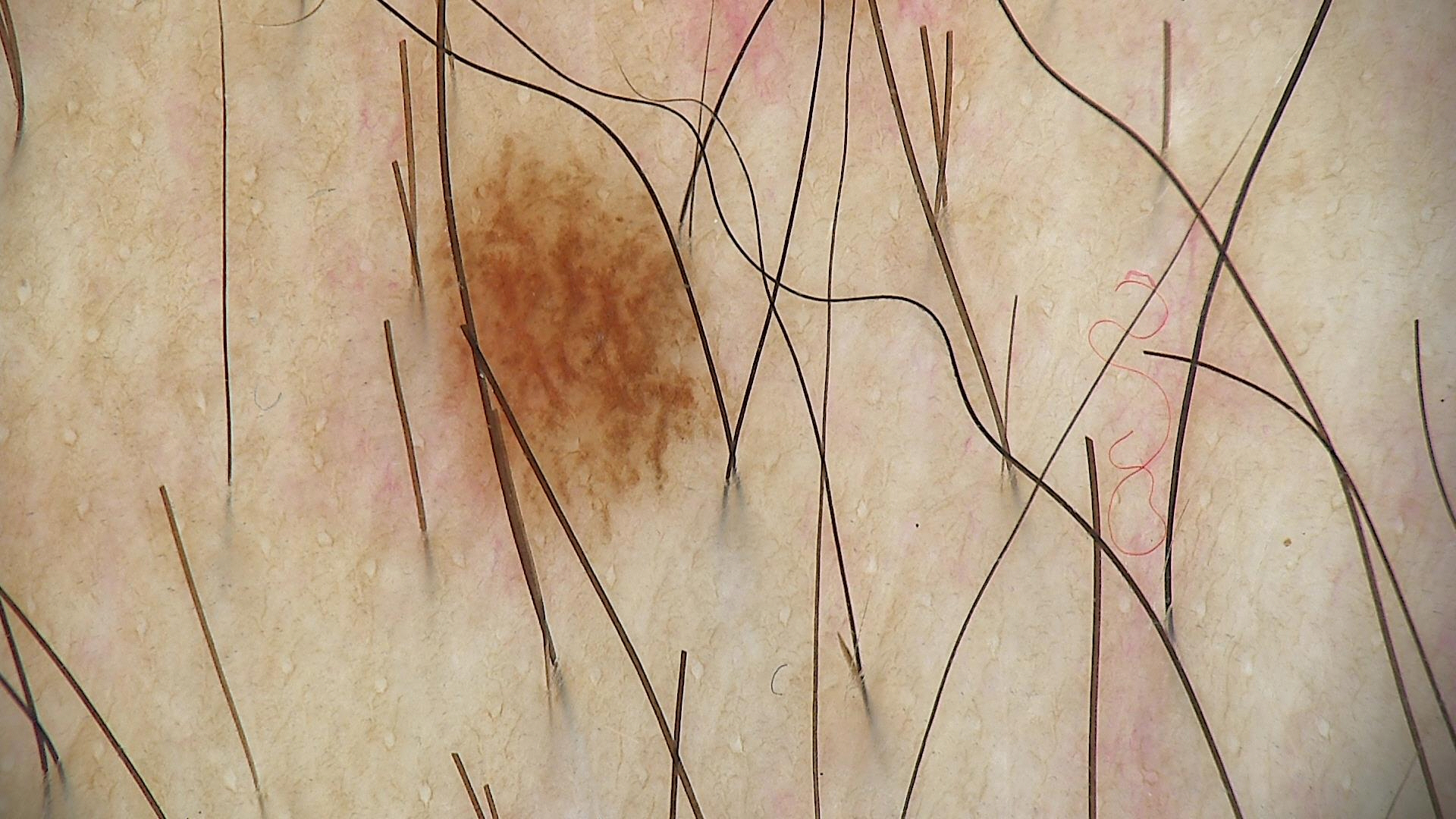Diagnosed as a dysplastic junctional nevus.